A male subject roughly 70 years of age. Recorded as Fitzpatrick skin type II. A clinical overview photograph of a skin lesion.
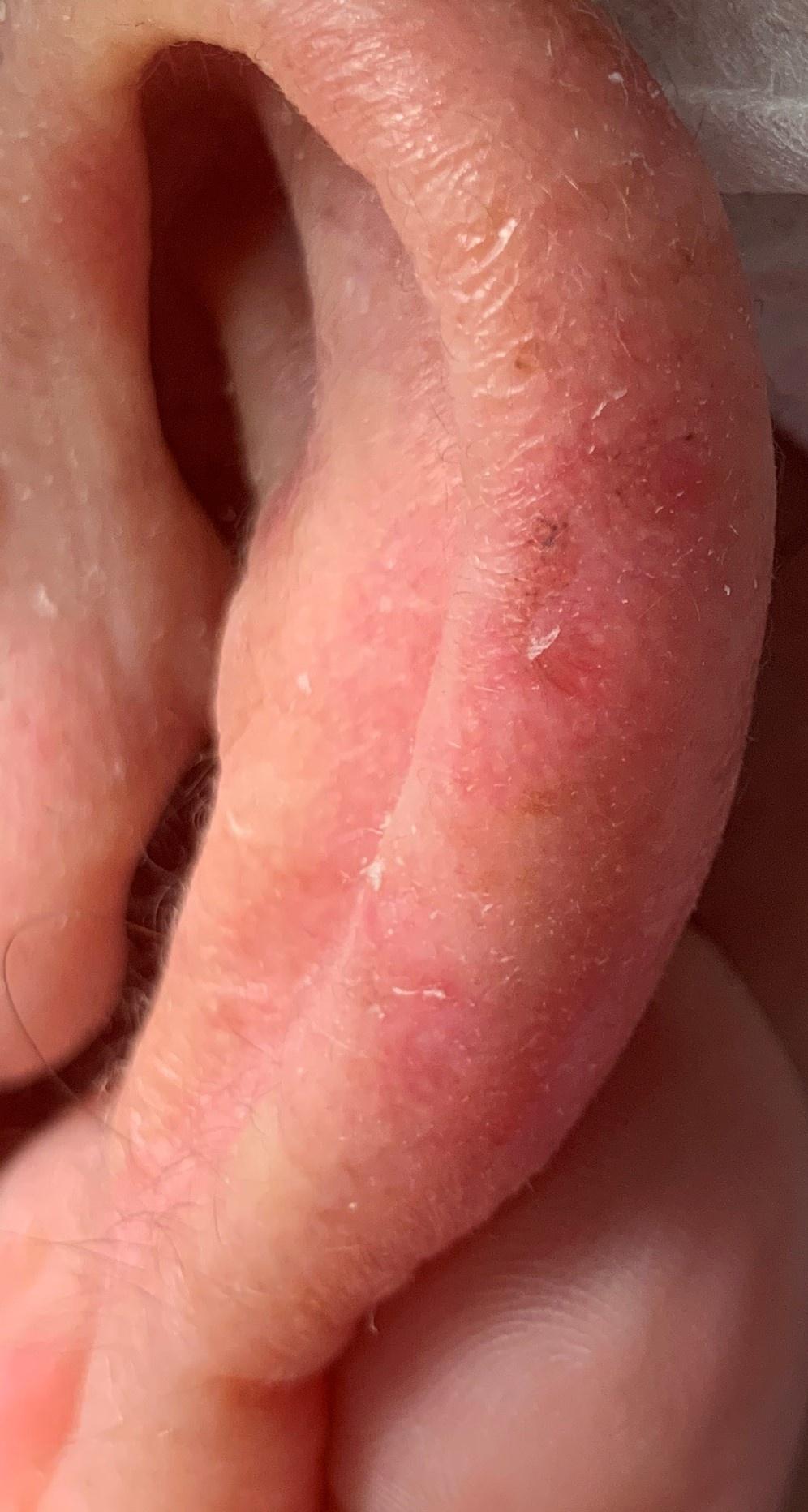lesion_location:
  region: the head or neck
diagnosis:
  name: Basal cell carcinoma
  malignancy: malignant
  confirmation: histopathology
  lineage: adnexal